A skin lesion imaged with a dermatoscope.
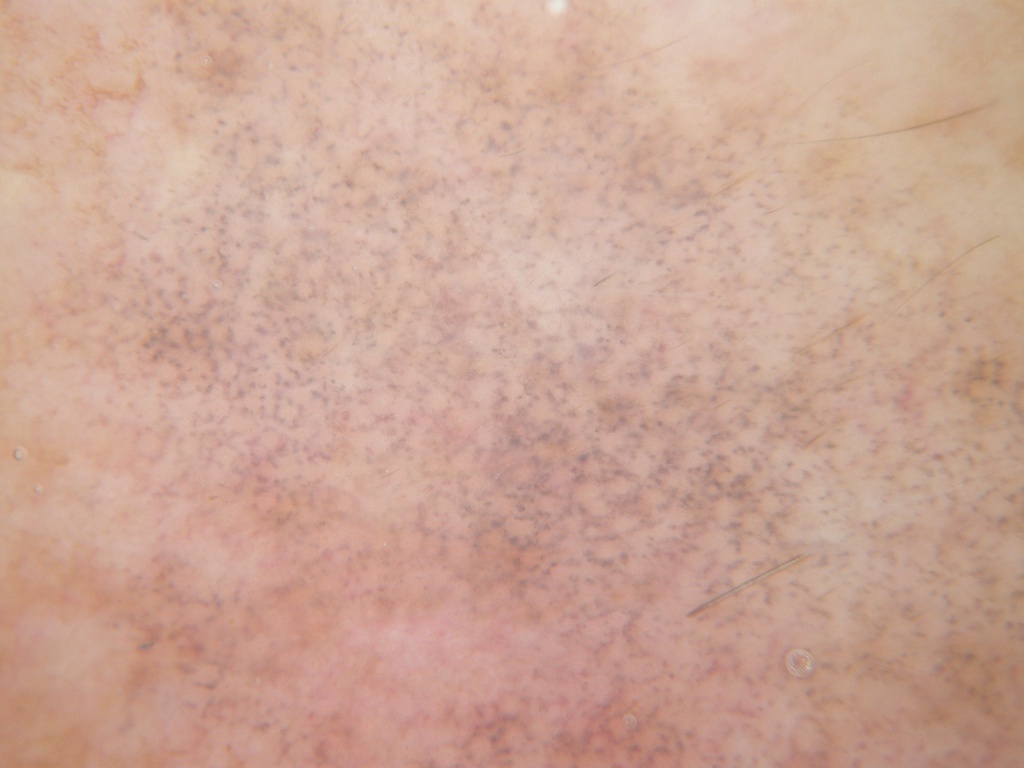Findings: The lesion extends across almost the whole field of view. Conclusion: The clinical diagnosis was a benign lesion.